The patient is a female aged 50–59; the lesion is described as raised or bumpy; located on the leg; the photograph was taken at a distance; Fitzpatrick II — 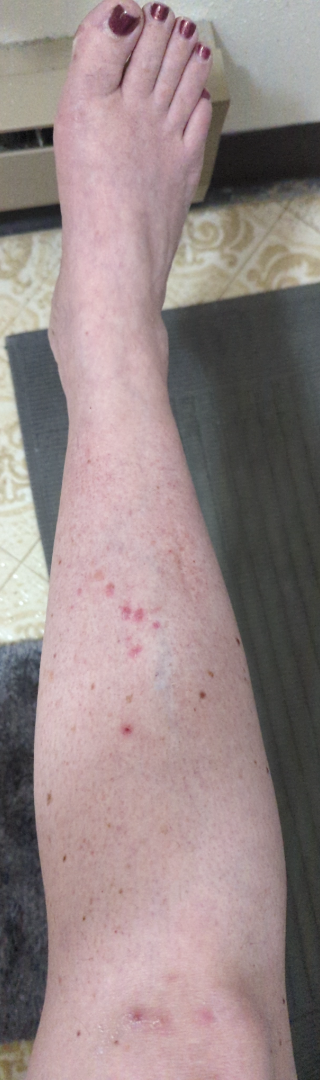Pigmented purpuric eruption (considered); Stasis Dermatitis (considered); Eczema (considered).